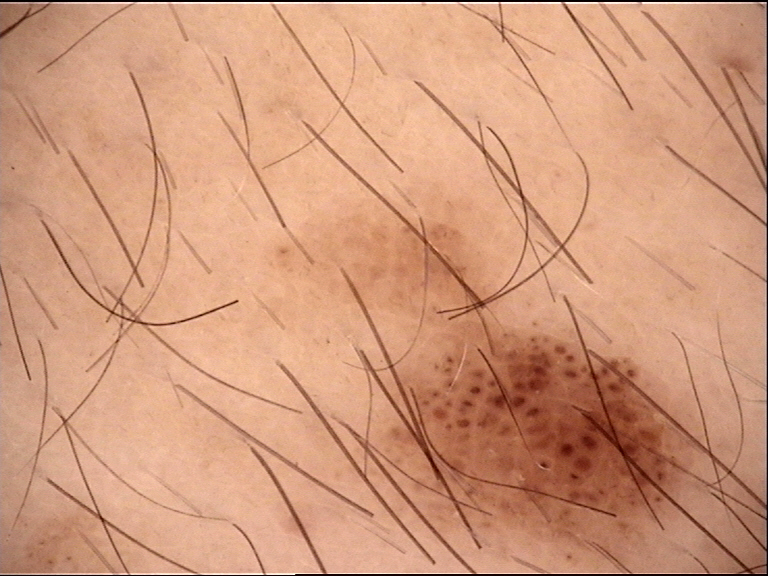Findings:
* assessment: congenital compound nevus (expert consensus)